The photo was captured at an angle. Female patient, age 18–29. The affected area is the back of the hand: 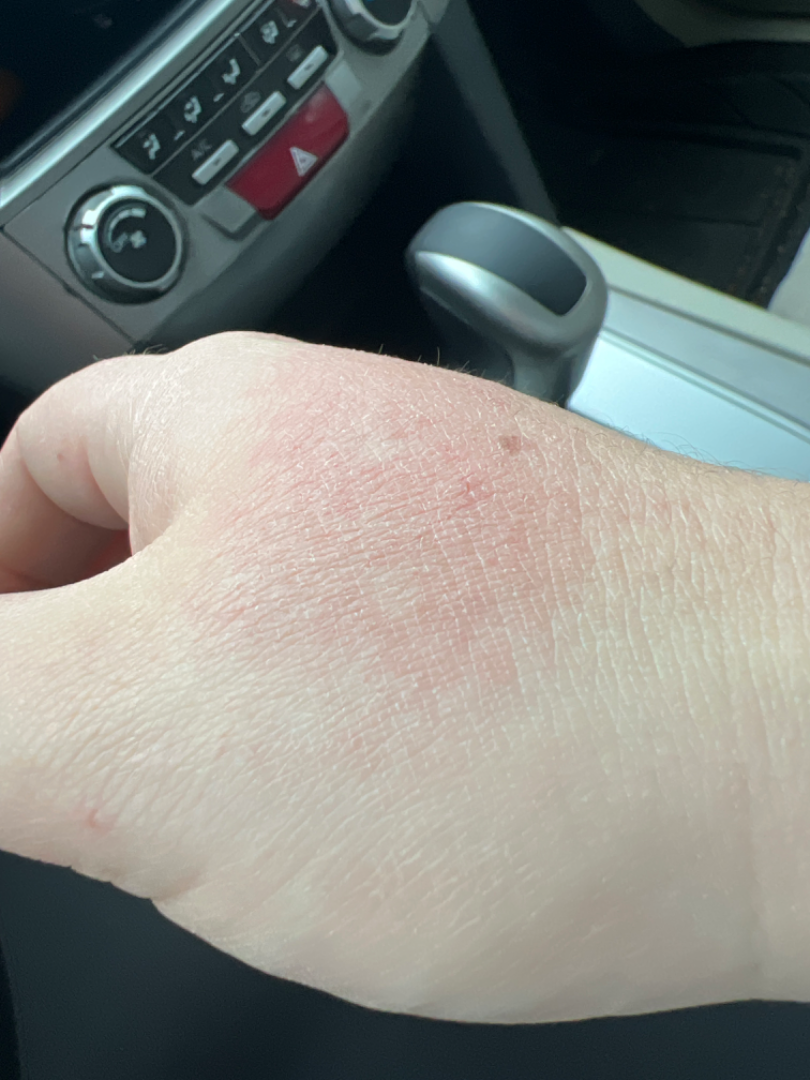Findings:
The favored diagnosis is Irritant Contact Dermatitis; possibly Allergic Contact Dermatitis.